A male subject in their early 70s. History notes prior skin cancer (patient or family) and pesticide exposure. Recorded as Fitzpatrick skin type III — 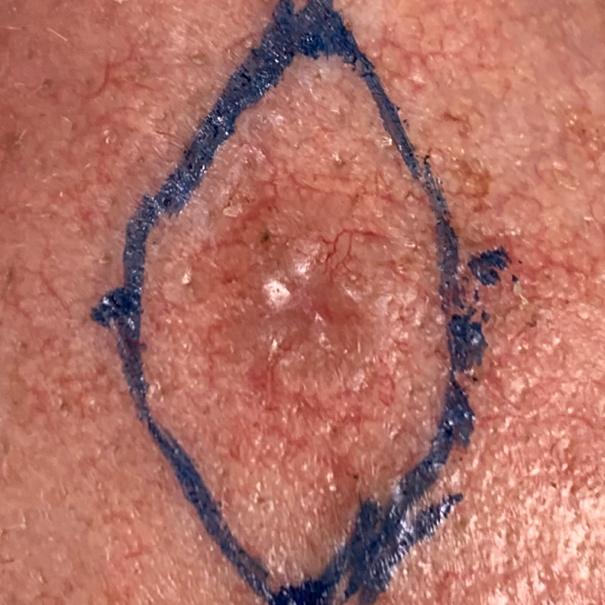The lesion was found on the face.
The lesion measures approximately 10 × 7 mm.
Per patient report, the lesion has changed, has grown, and is elevated.
Histopathologically confirmed as a malignant skin lesion — a basal cell carcinoma.